The head or neck, front of the torso and arm are involved. The photograph is a close-up of the affected area. Male contributor, age 40–49:
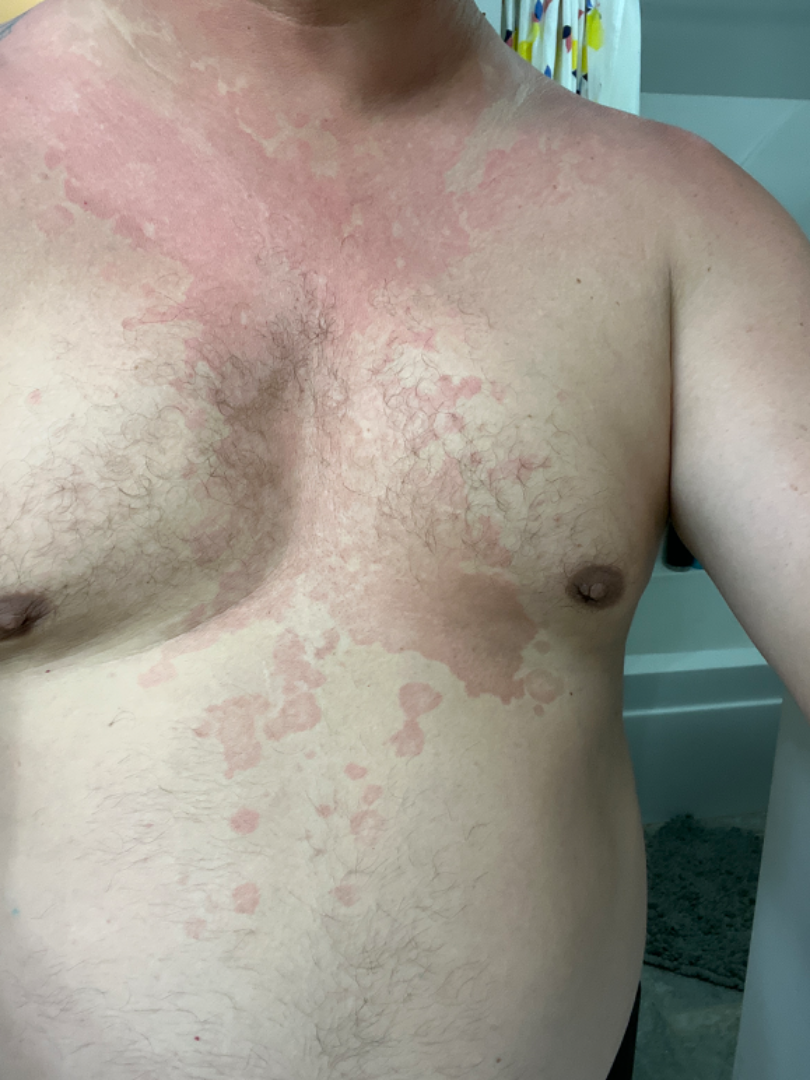self-categorized as = a rash | reported symptoms = enlargement, bothersome appearance and itching | impression = favoring Tinea Versicolor; a more distant consideration is Drug-induced pellagra; less likely is Eczema.